A female patient, aged approximately 15 · dermoscopy of a skin lesion: 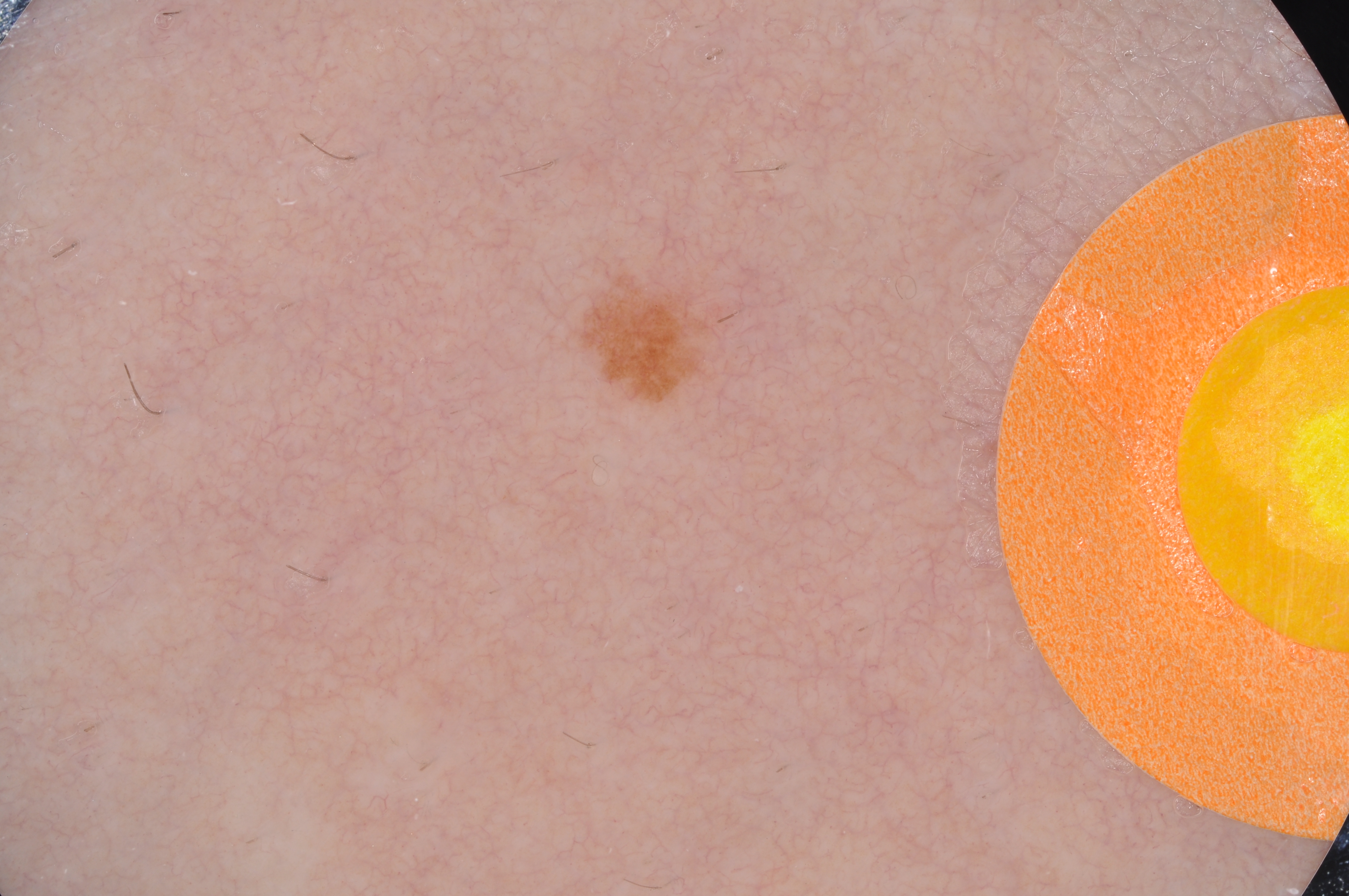Findings:
A small lesion within a wider field of skin. Dermoscopic review identifies pigment network, with no streaks, milia-like cysts, or negative network. As (left, top, right, bottom), lesion location: <bbox>570, 260, 736, 409</bbox>.
Assessment:
Clinically diagnosed as a melanocytic nevus, a benign lesion.